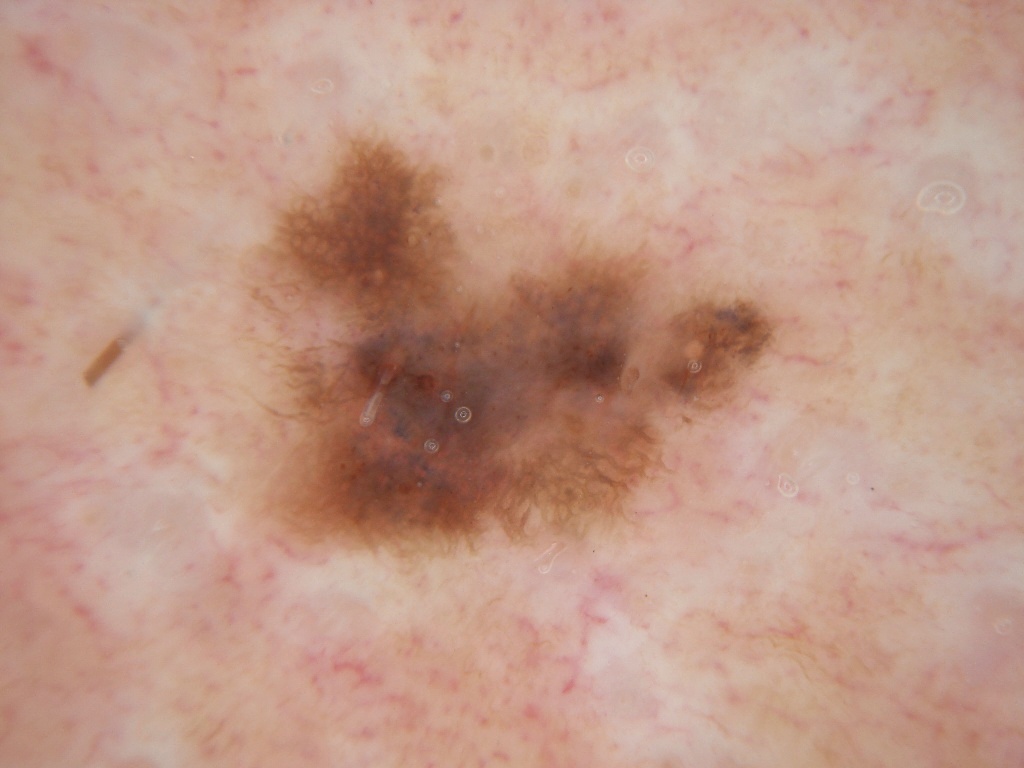patient = male, in their 70s
modality = dermatoscopic image of a skin lesion
bounding box = (235, 129, 811, 564)
size = moderate
features = pigment network; absent: milia-like cysts, streaks, globules, and negative network
diagnosis = a melanocytic nevus, a benign skin lesion